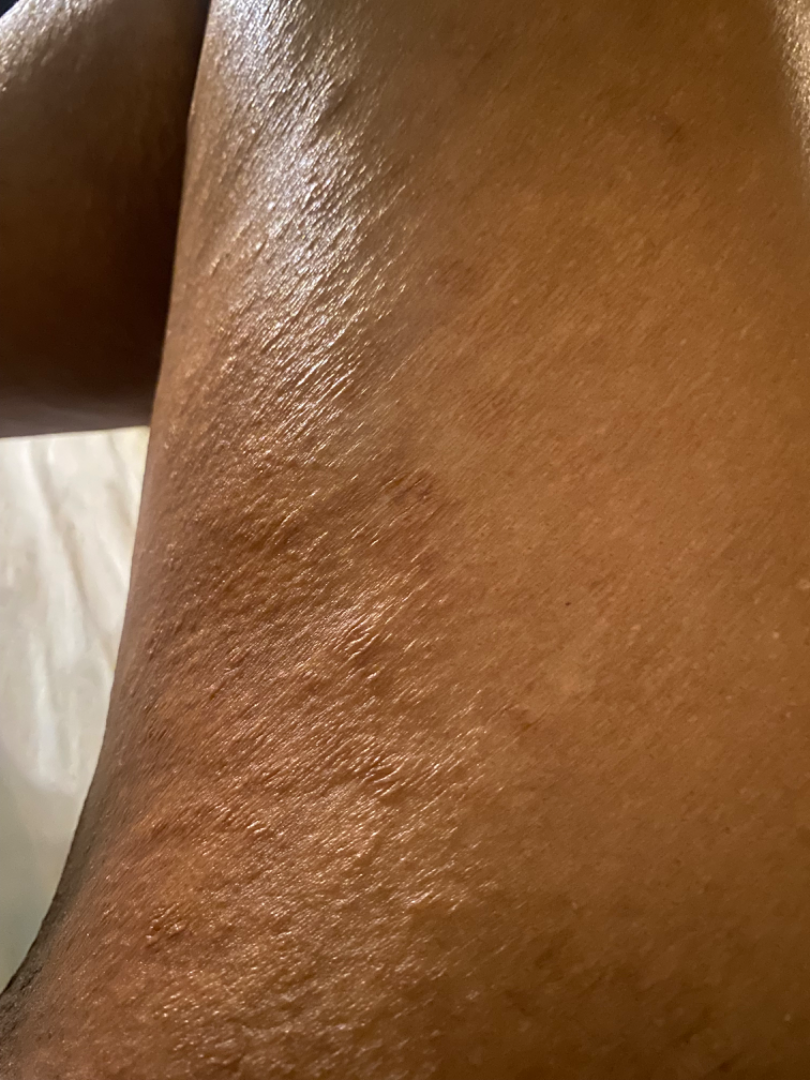Background:
Located on the leg. This is a close-up image.
Findings:
The differential is split between Cutaneous T Cell Lymphoma, Psoriasis and Eczema.